Dermoscopy of a skin lesion: 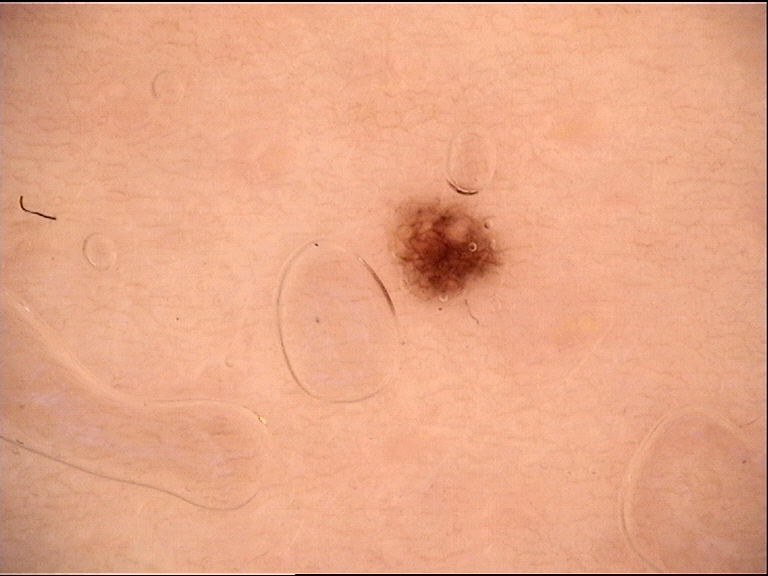diagnosis = dysplastic junctional nevus (expert consensus).